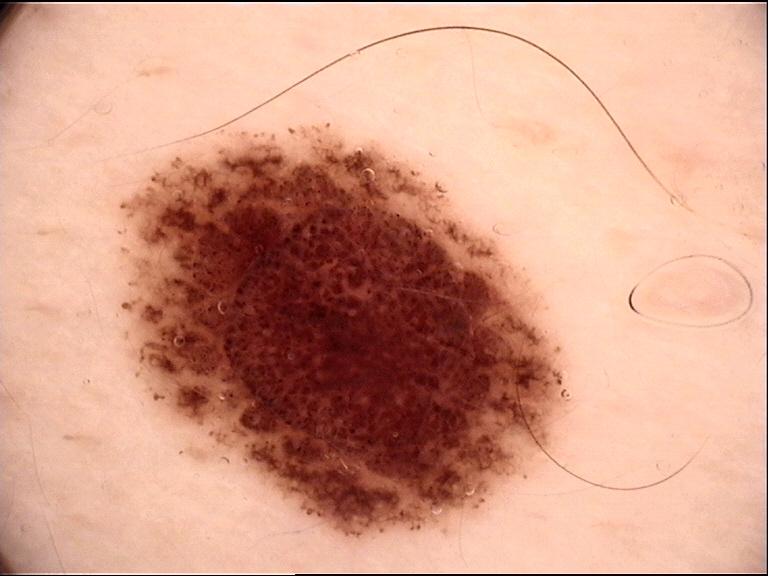Findings:
A dermatoscopic image of a skin lesion.
Conclusion:
Consistent with a benign lesion — a dysplastic compound nevus.